The patient indicates the lesion is flat. The front of the torso is involved. This image was taken at an angle. The lesion is associated with burning and pain. The patient indicates the condition has been present for one to four weeks: 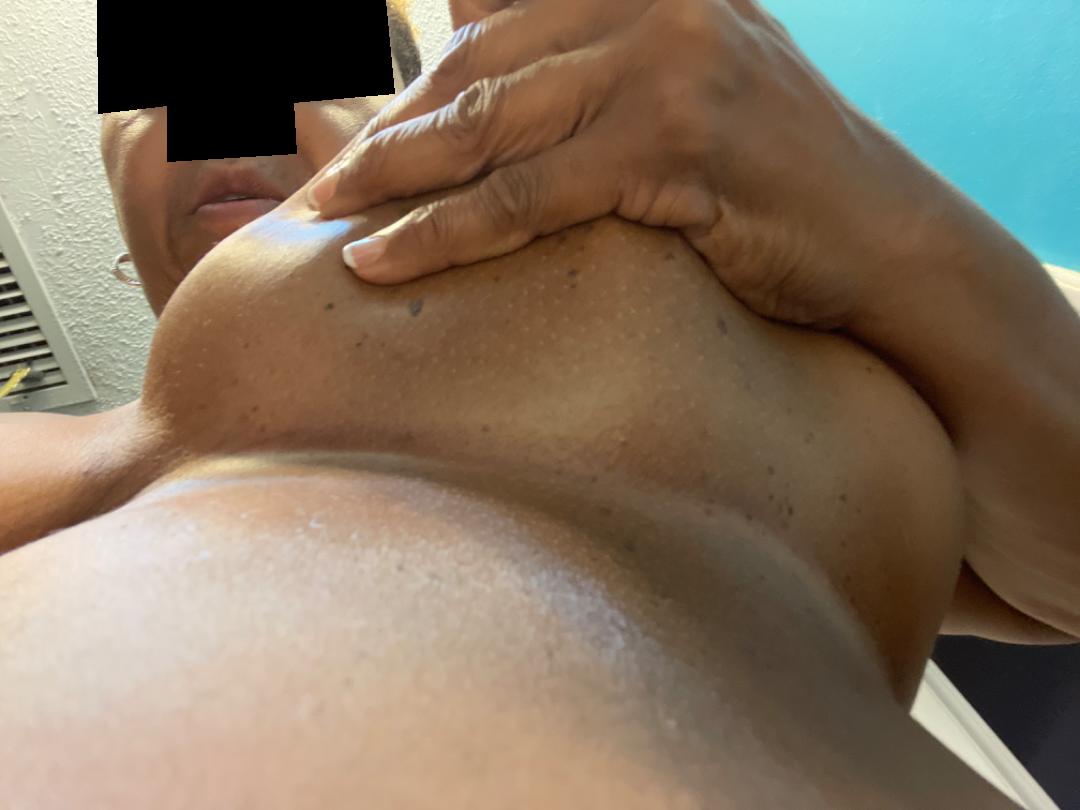The dermatologist could not determine a likely condition from the photograph alone.